The photo was captured at an angle; the affected area is the leg; female contributor, age 18–29 — 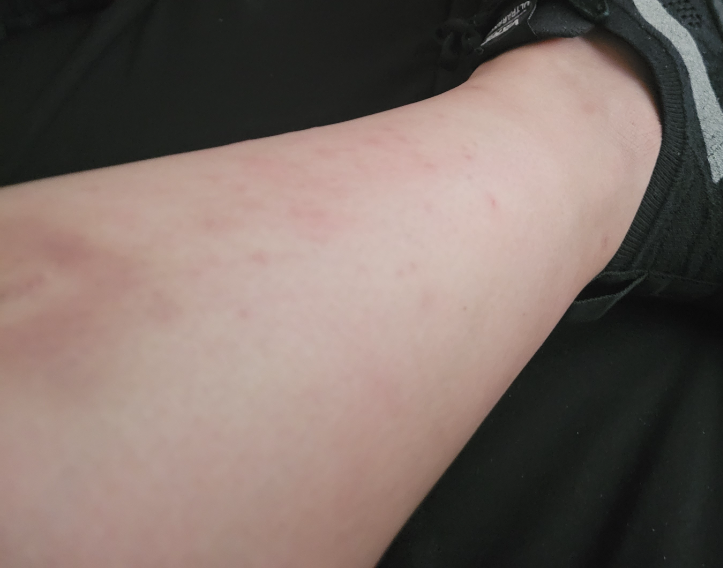Assessment: The case was indeterminate on photographic review. Clinical context: The patient described the issue as a rash. FST III. The condition has been present for about one day.